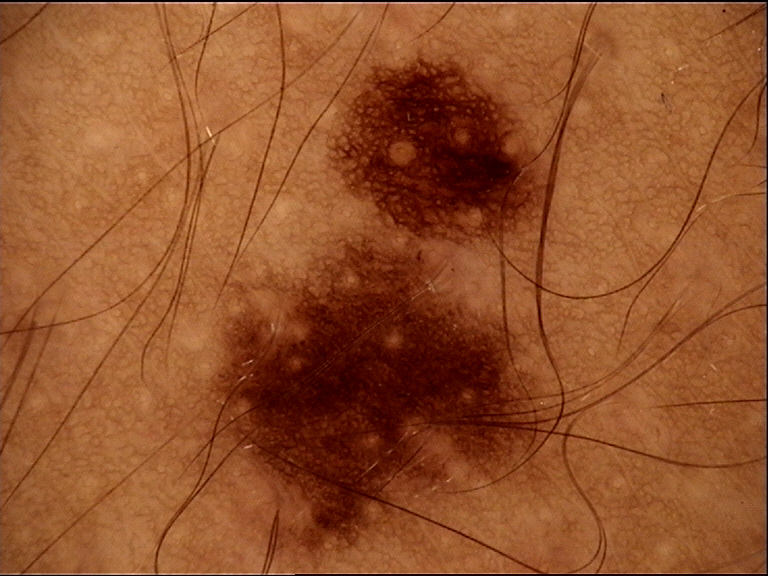{
  "diagnosis": {
    "name": "dysplastic junctional nevus",
    "code": "jd",
    "malignancy": "benign",
    "super_class": "melanocytic",
    "confirmation": "expert consensus"
  }
}